An image taken at a distance · the subject is 50–59, female · the head or neck, arm and front of the torso are involved.
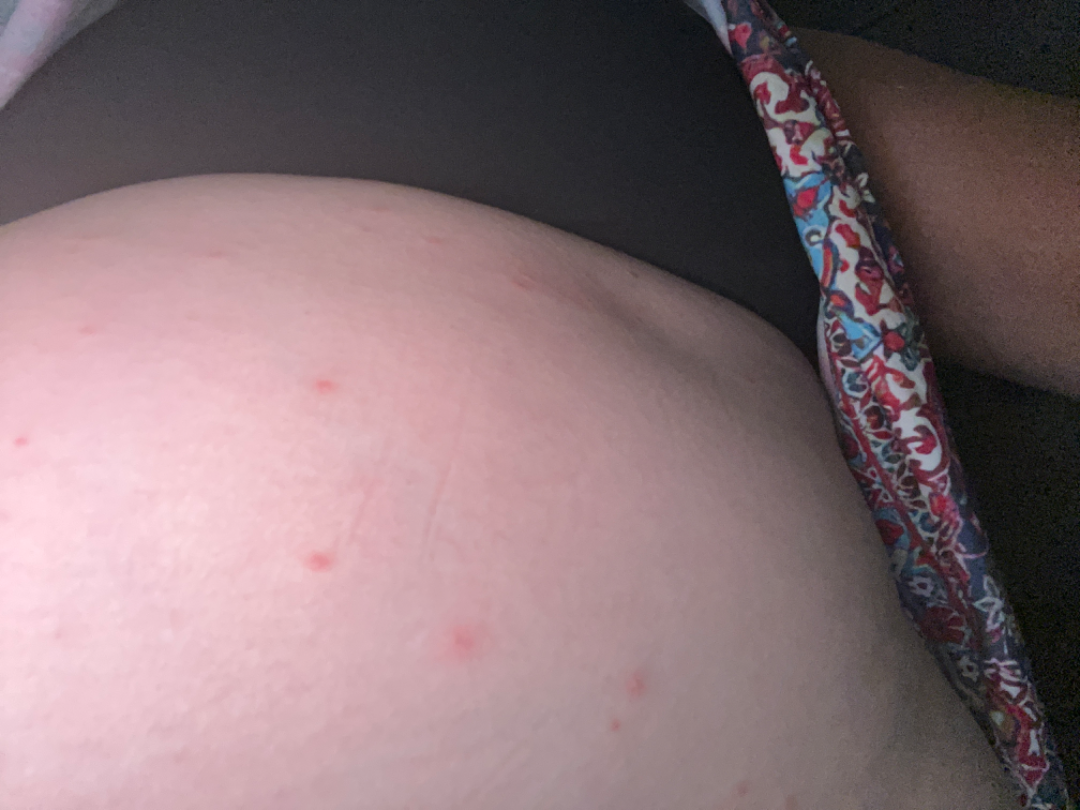The case was difficult to assess from the available photograph. The patient reports the condition has been present for about one day. No associated systemic symptoms reported. The patient reports the lesion is fluid-filled and raised or bumpy. Symptoms reported: bothersome appearance and itching.